A skin lesion imaged with a dermatoscope.
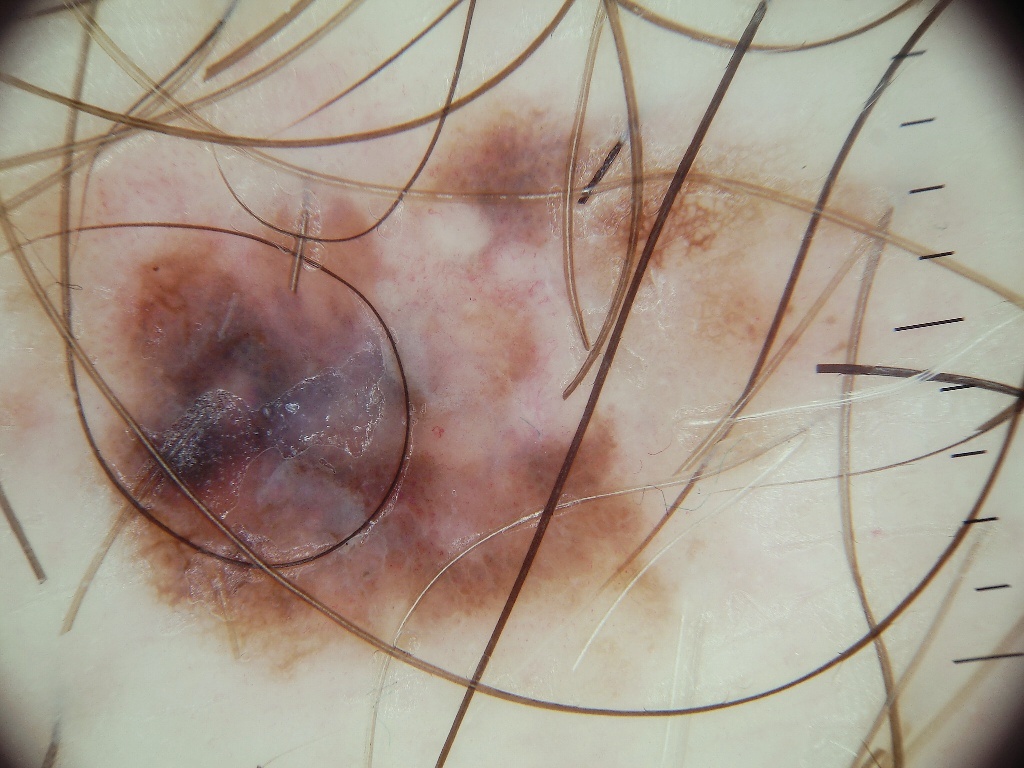Summary:
In (x1, y1, x2, y2) order, the lesion's extent is <box>10, 98, 909, 696</box>.
Conclusion:
Confirmed on histopathology as a skin cancer.